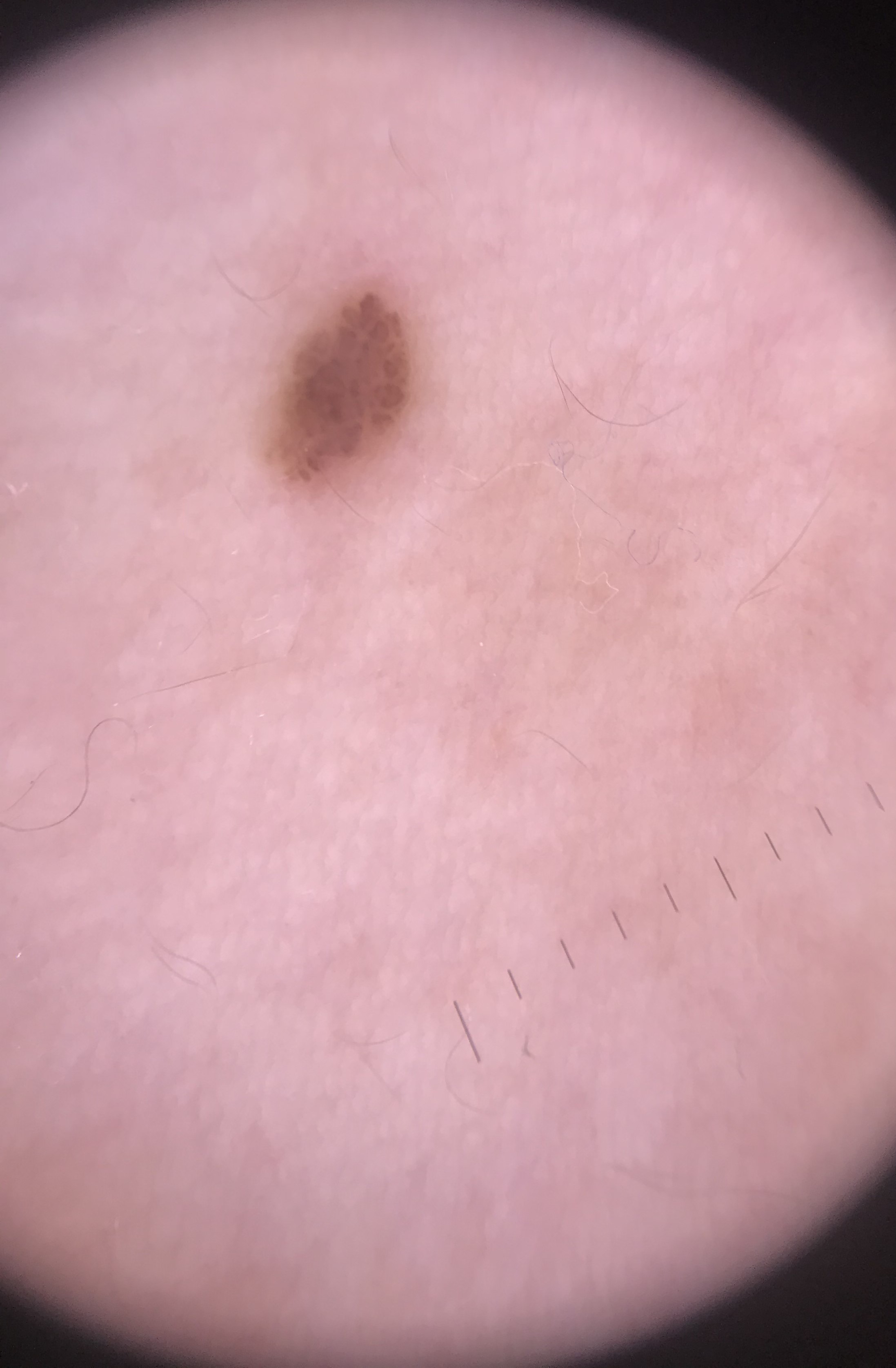image — dermoscopy
diagnostic label — compound nevus (expert consensus)